The patient is 50–59, male · the patient considered this a rash · this image was taken at a distance · Fitzpatrick III; non-clinician graders estimated Monk Skin Tone 2 · texture is reported as raised or bumpy · the affected area is the leg and top or side of the foot · reported duration is three to twelve months:
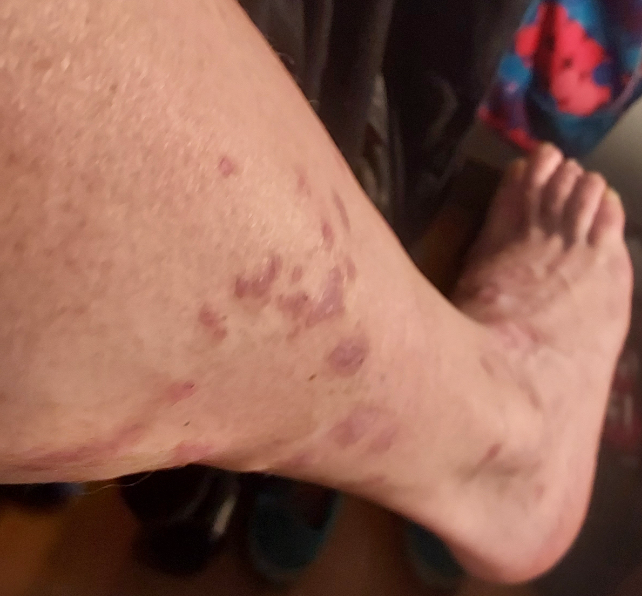Q: What is the differential diagnosis?
A: Lichen planus/lichenoid eruption and Nodular vasculitis were considered with similar weight; a more distant consideration is Psoriasis; less probable is Eczema; less likely is Pseudolymphoma